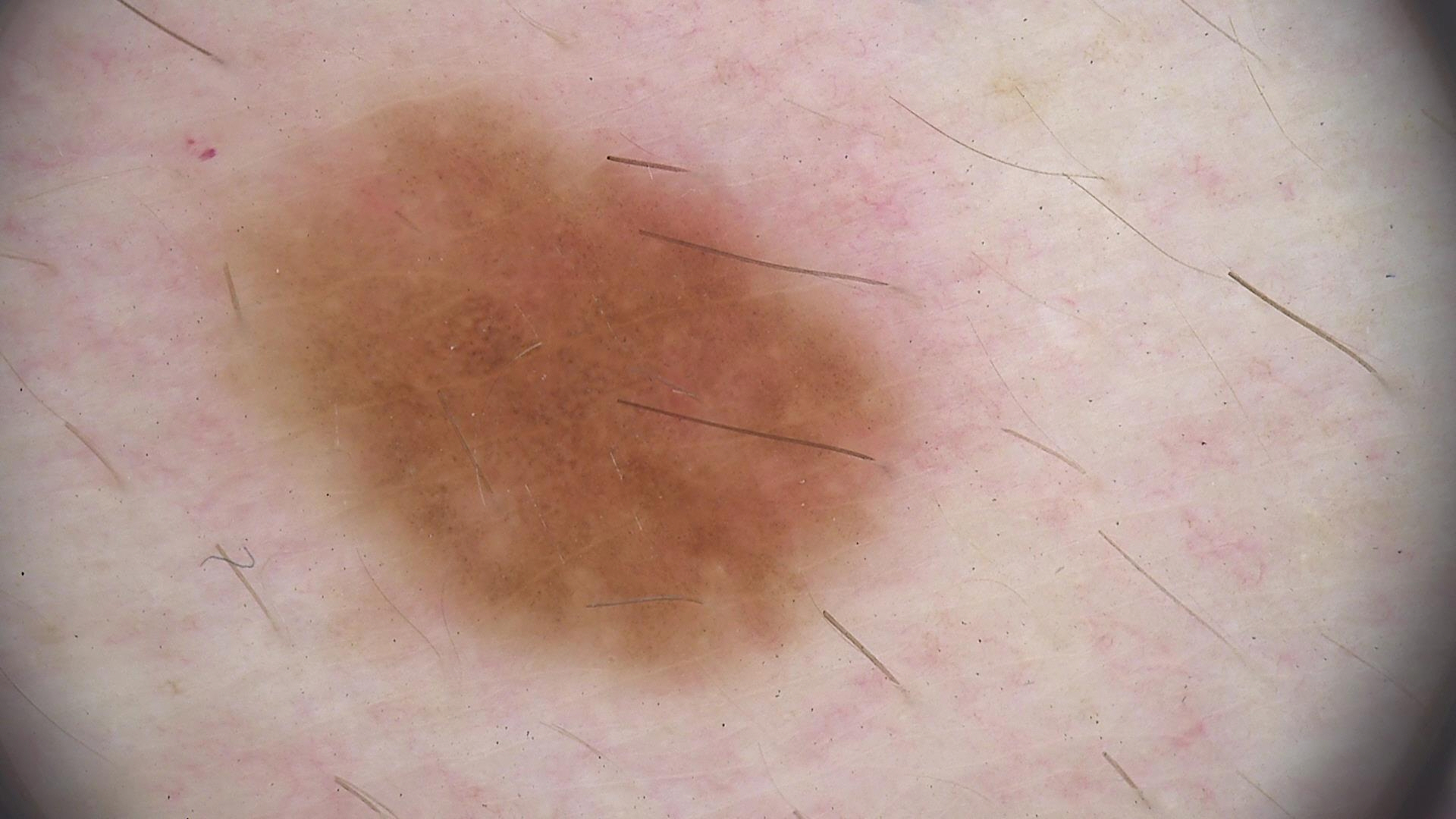Classified as a dysplastic junctional nevus.